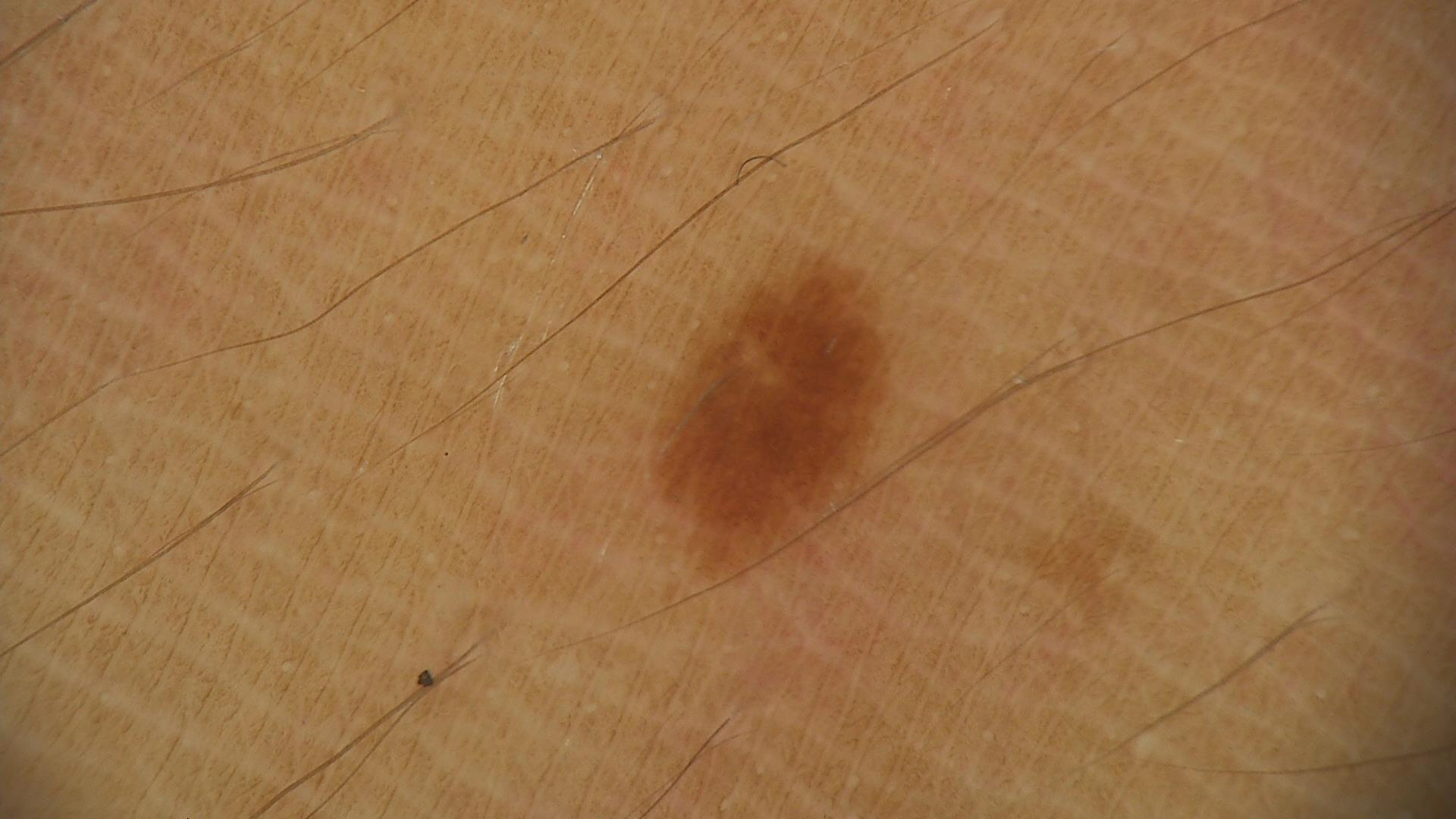The diagnosis was a junctional nevus.